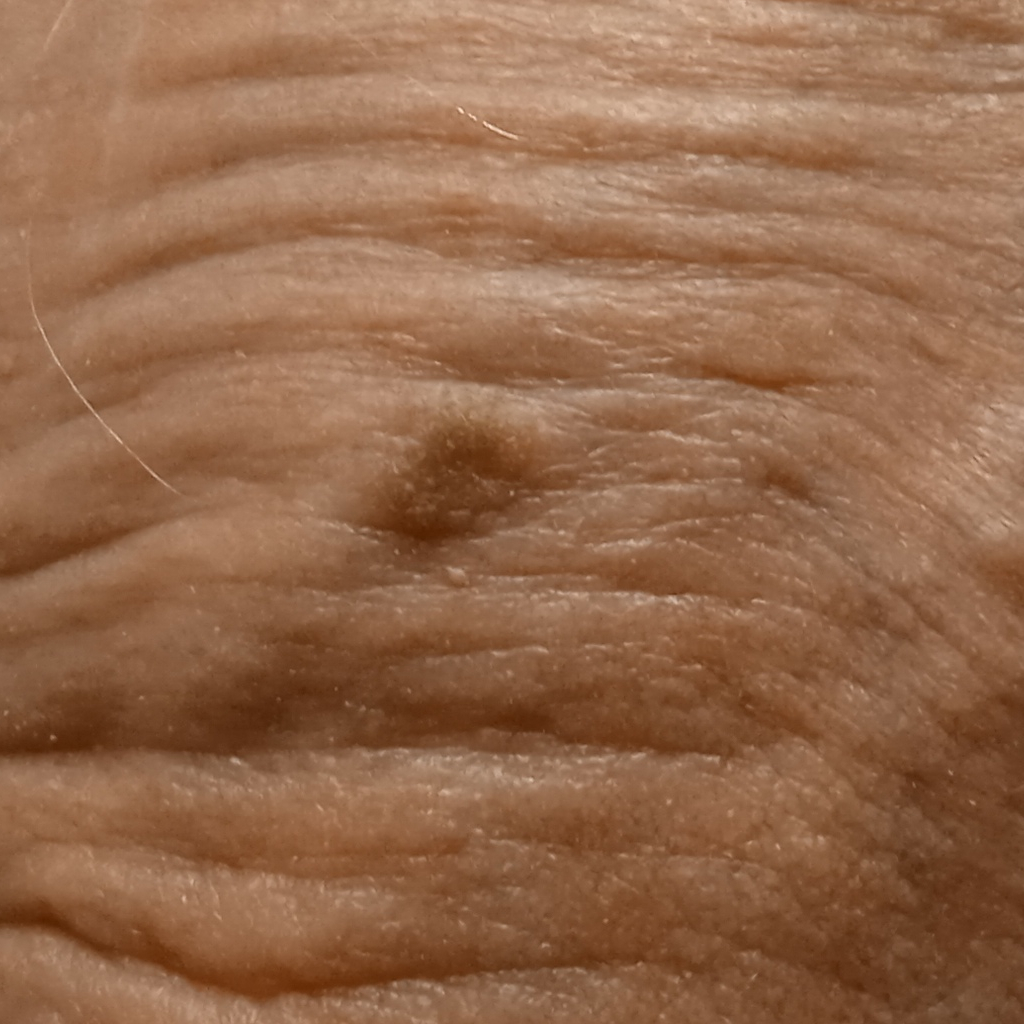{"patient": {"age": 89, "sex": "male"}, "image": "clinical photo", "lesion_size": {"diameter_mm": 6.4}, "diagnosis": {"name": "actinic keratosis", "malignancy": "benign"}}